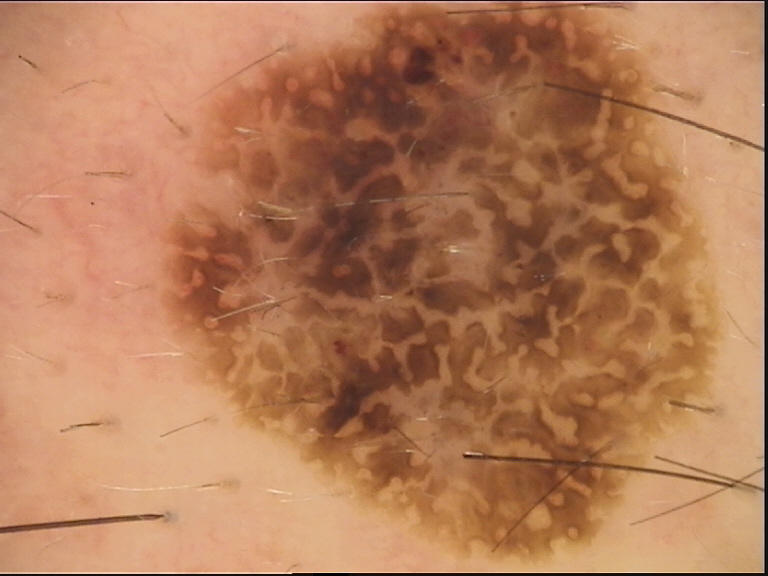Case:
• image type — dermoscopy
• lesion type — keratinocytic
• class — seborrheic keratosis (expert consensus)